Symptoms reported: itching, burning, bothersome appearance, pain and darkening · a close-up photograph · the condition has been present for less than one week · texture is reported as raised or bumpy · self-categorized by the patient as a rash · no relevant systemic symptoms.
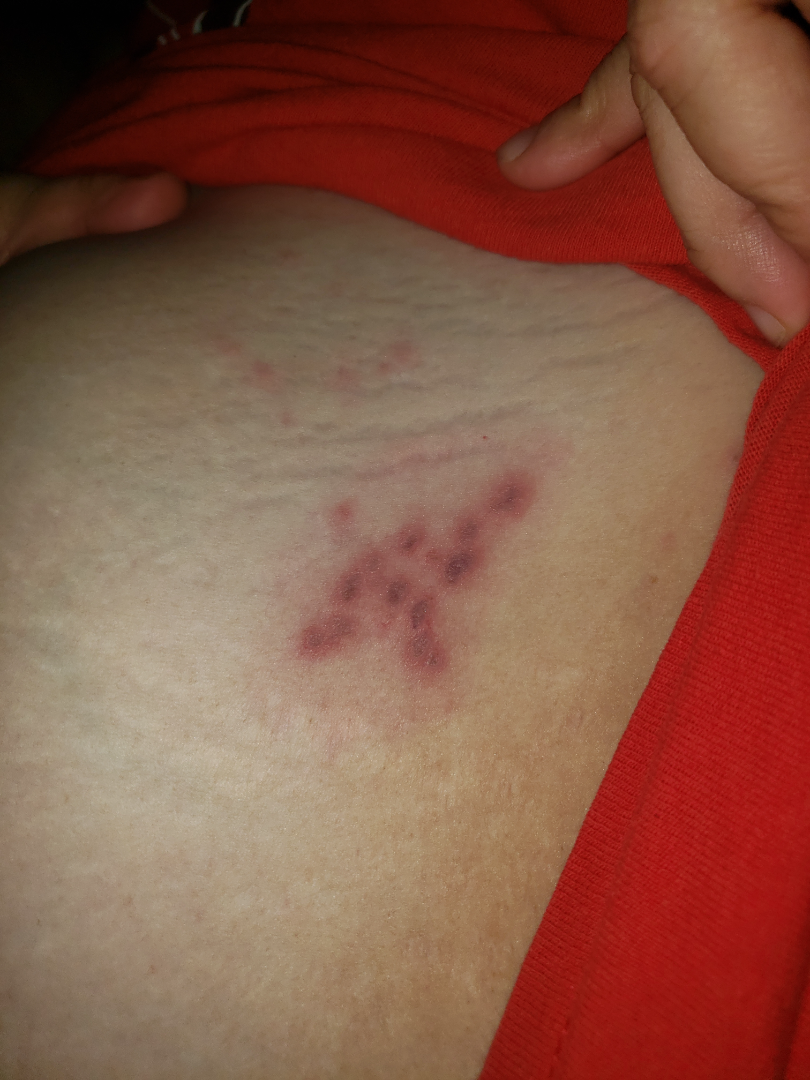On remote review of the image, favoring Herpes Simplex; also consider Herpes Zoster.